The patient is a male about 50 years old. A dermoscopic view of a skin lesion.
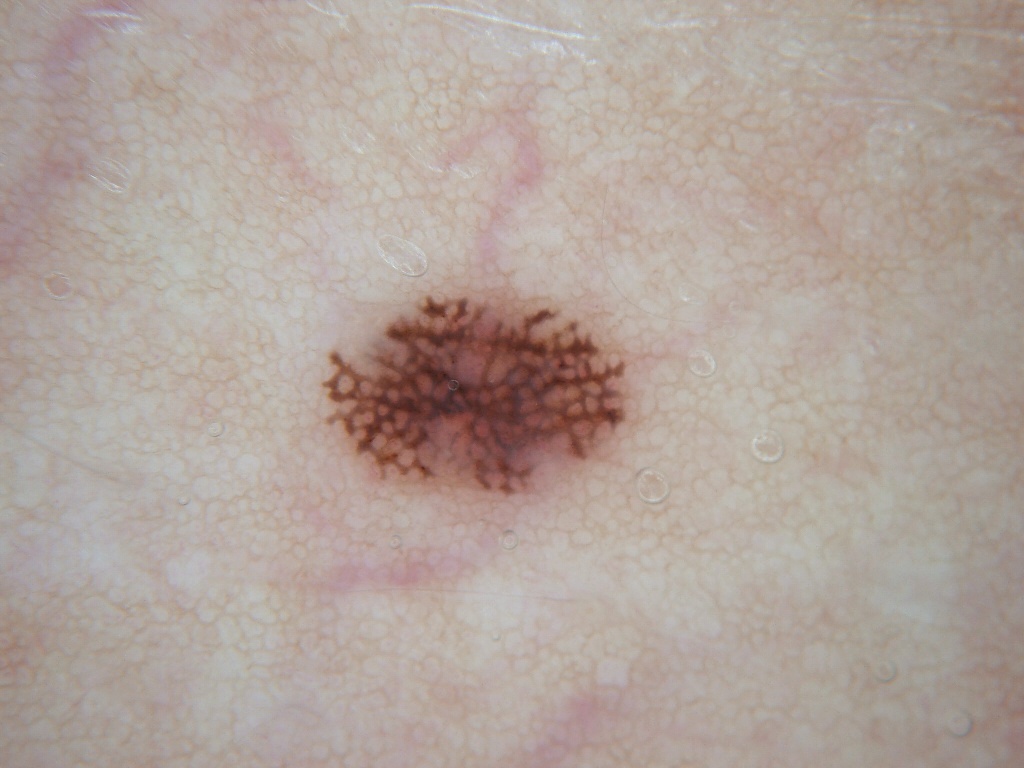Dermoscopy demonstrates pigment network. As (left, top, right, bottom), the lesion occupies the region 327 288 628 501. Clinically diagnosed as a melanocytic nevus.